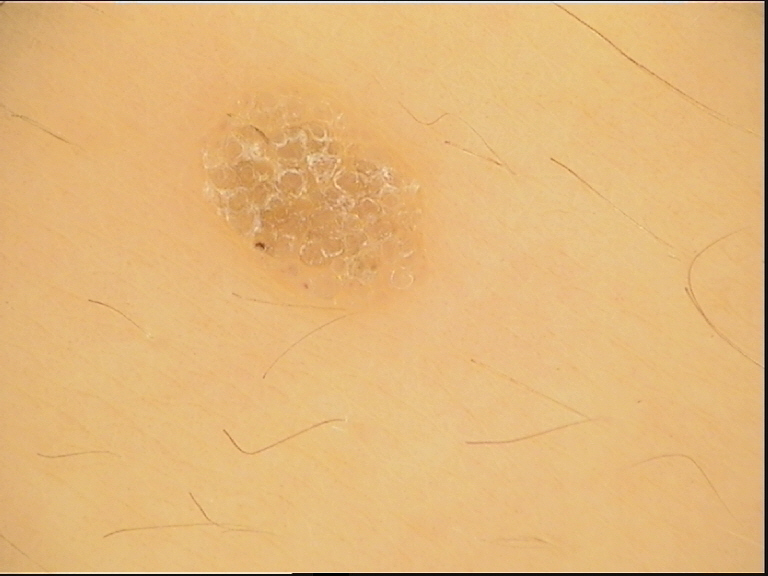<dermoscopy>
  <lesion_type>
    <main_class>keratinocytic</main_class>
  </lesion_type>
  <diagnosis>
    <name>seborrheic keratosis</name>
    <code>sk</code>
    <malignancy>benign</malignancy>
    <super_class>non-melanocytic</super_class>
    <confirmation>expert consensus</confirmation>
  </diagnosis>
</dermoscopy>